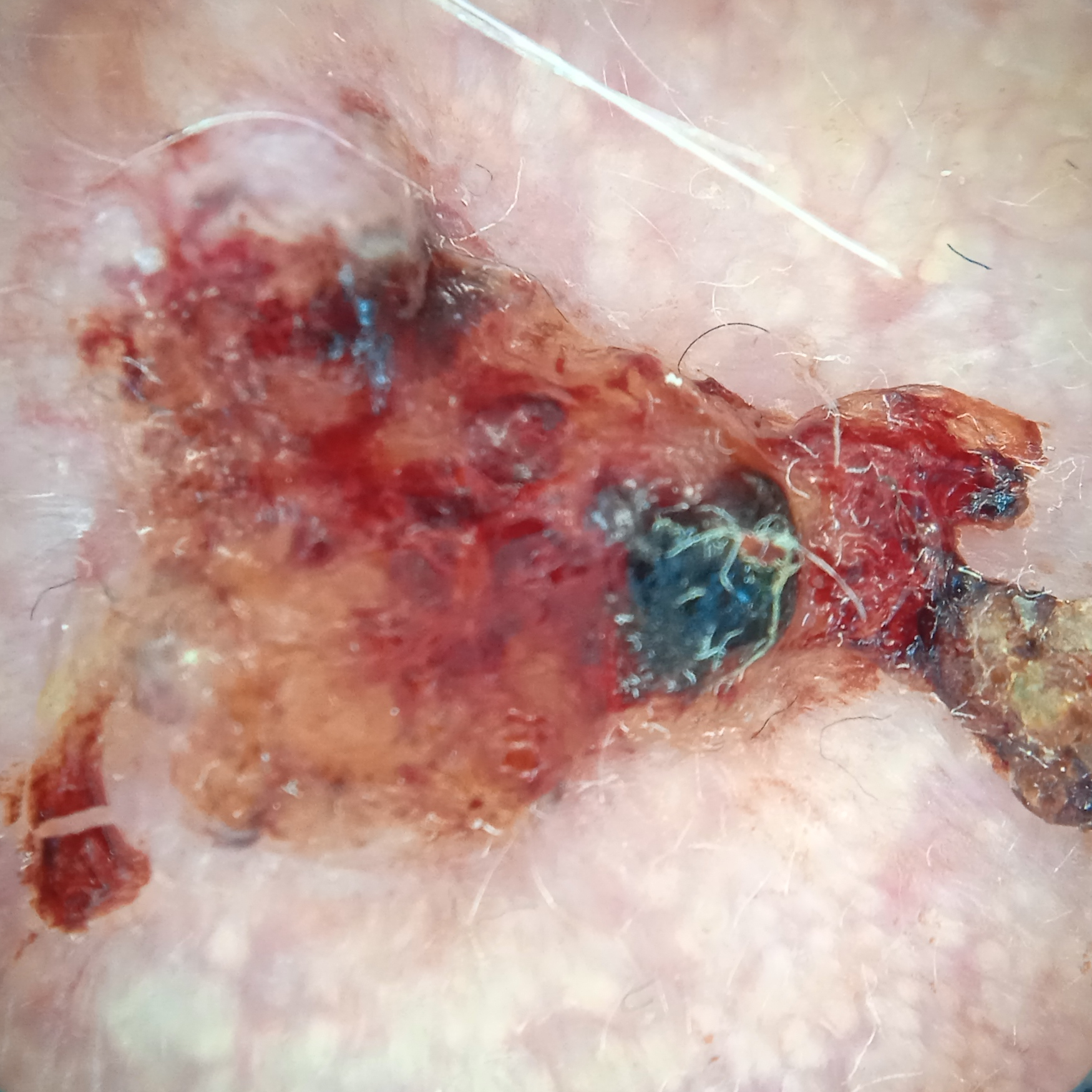Summary:
The patient says their skin reddens painfully with sun exposure. A male subject aged 89. A dermoscopy image of a skin lesion. Located on the face.
Diagnosis:
Confirmed on histopathology as a basal cell carcinoma, following excision, with tumor thickness 2 mm.